A dermoscopic view of a skin lesion · the patient is a male about 45 years old: 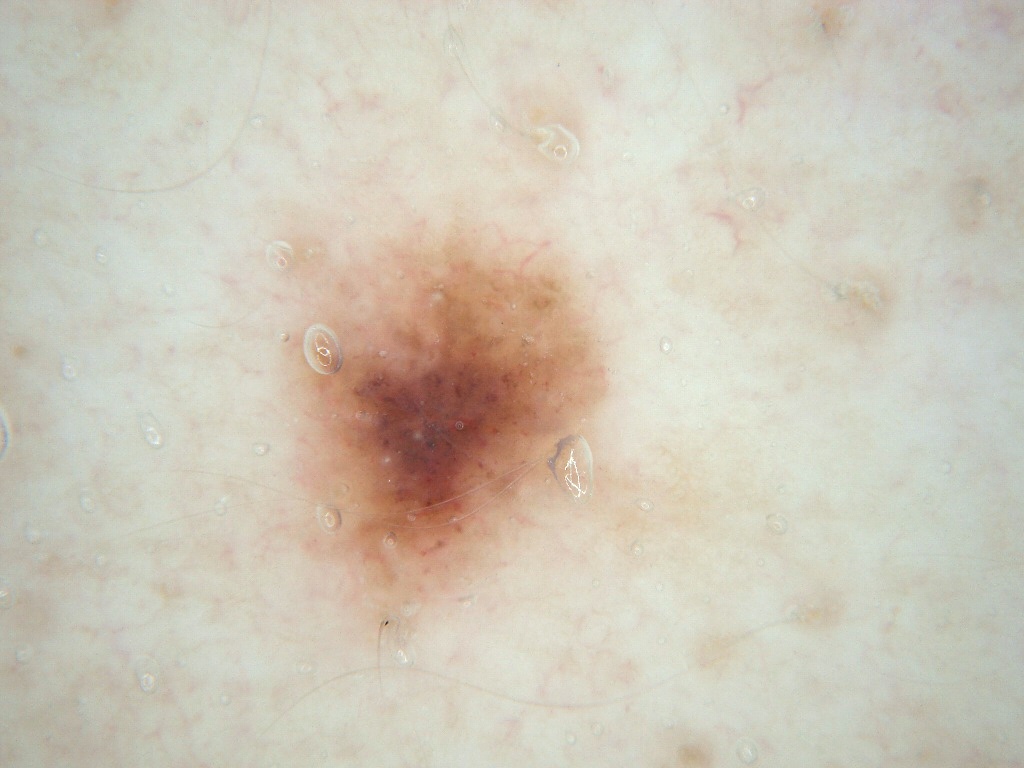A mid-sized lesion within the field. The lesion's extent is x1=272, y1=229, x2=605, y2=637. On dermoscopy, the lesion shows milia-like cysts, with no pigment network, streaks, negative network, or globules. Consistent with a melanocytic nevus.